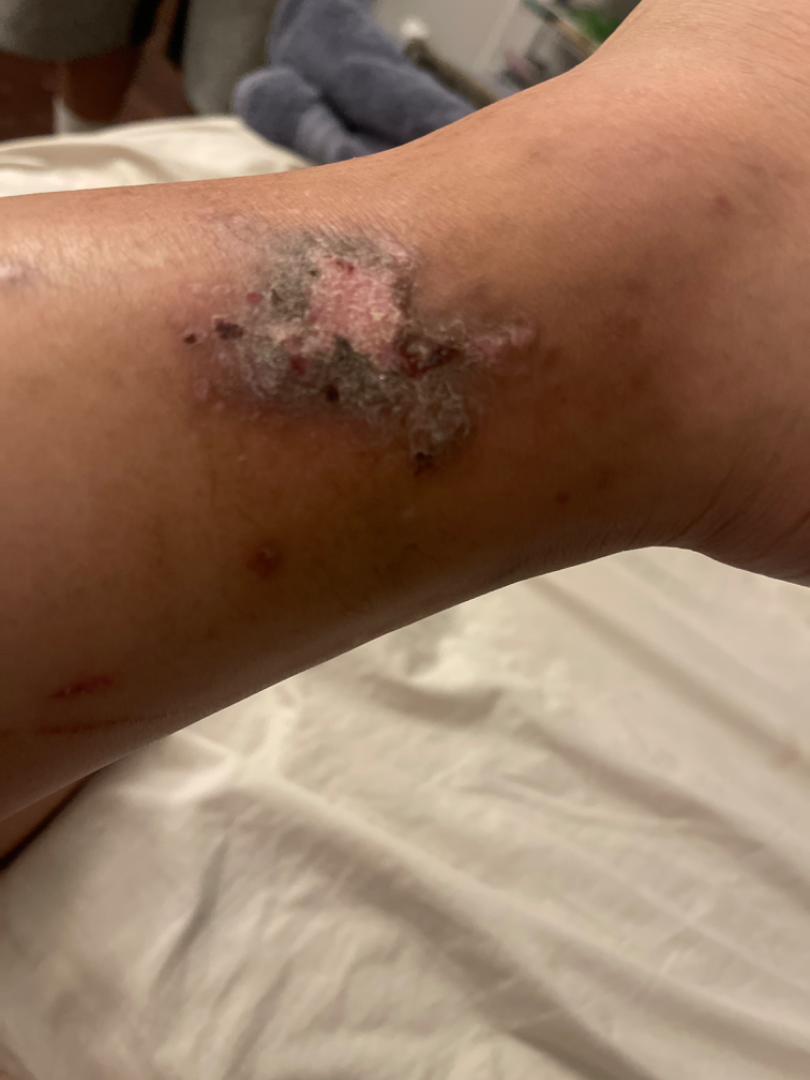Texture is reported as rough or flaky.
Reported lesion symptoms include pain, bleeding, itching and bothersome appearance.
Self-categorized by the patient as a rash.
The patient is female.
Present for since childhood.
A close-up photograph.
The reviewing dermatologist's impression was: Lichen Simplex Chronicus (weight 0.55); Deep fungal infection (weight 0.27); SCC/SCCIS (weight 0.18).